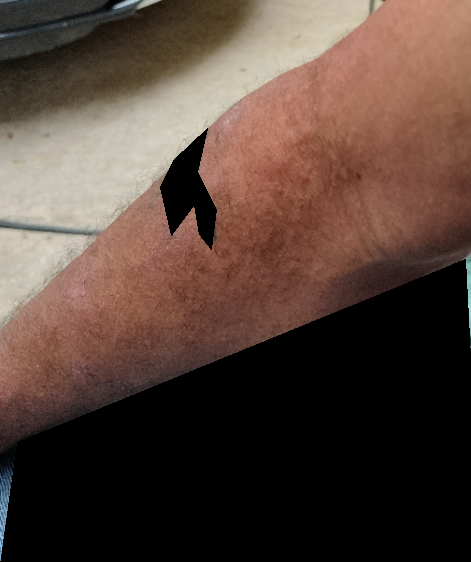Notes:
* lesion symptoms · itching
* history · less than one week
* systemic symptoms · none reported
* view · at a distance
* contributor · male
* body site · arm
* texture · raised or bumpy
* patient describes the issue as · a rash
* differential diagnosis · the impression is Eczema